This image was taken at a distance.
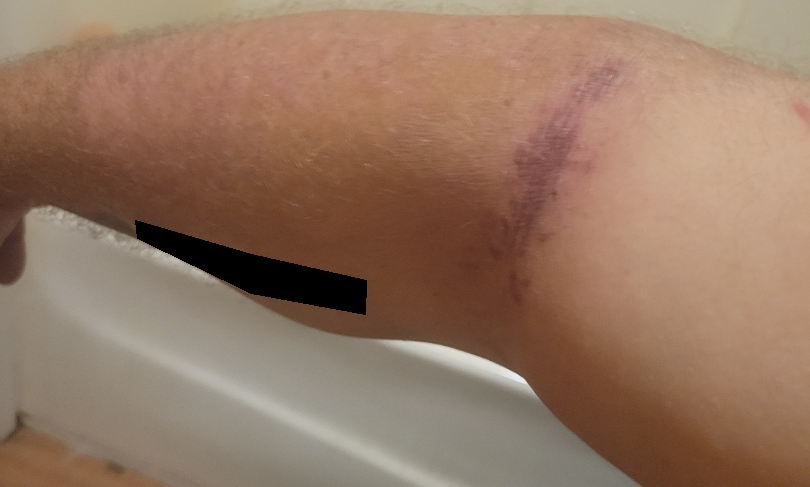Q: What is the differential diagnosis?
A: ecchymoses (1.00)